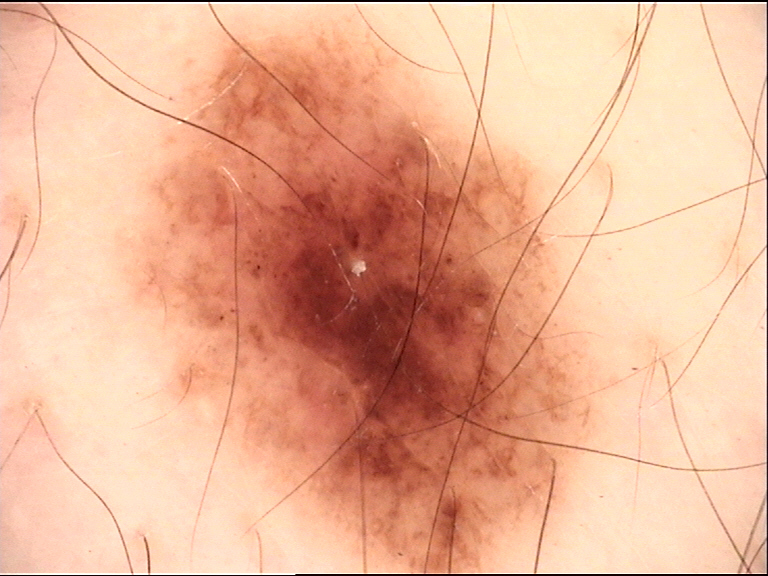Q: What is the diagnosis?
A: dysplastic junctional nevus (expert consensus)